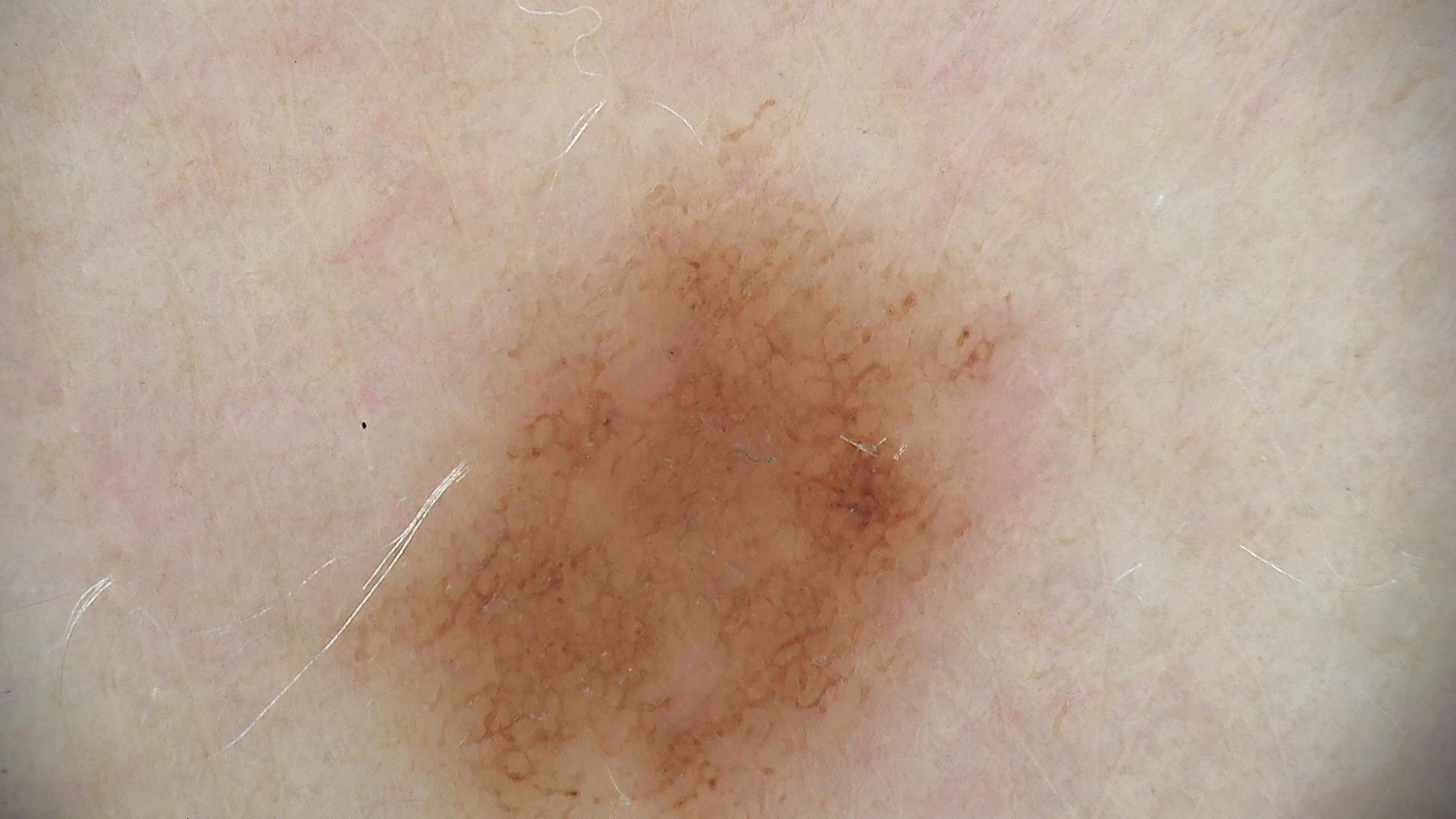Q: What is this lesion?
A: dysplastic junctional nevus (expert consensus)